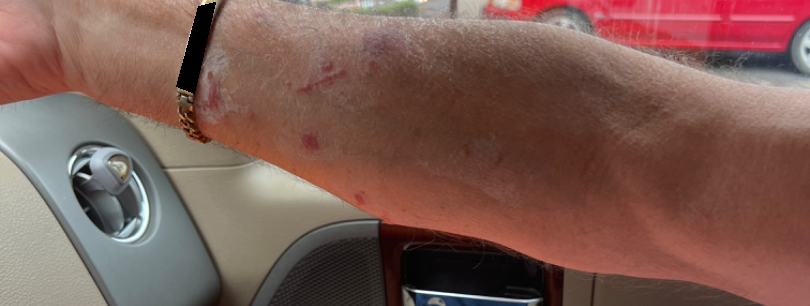* lesion texture · fluid-filled
* reported symptoms · itching
* contributor · male
* skin tone · Fitzpatrick II; human graders estimated Monk skin tone scale 3 (US pool) or 4 (India pool)
* present for · less than one week
* systemic symptoms · none reported
* patient describes the issue as · a rash
* shot type · at a distance
* site · arm and front of the torso
* differential · Allergic Contact Dermatitis and Contact dermatitis were considered with similar weight